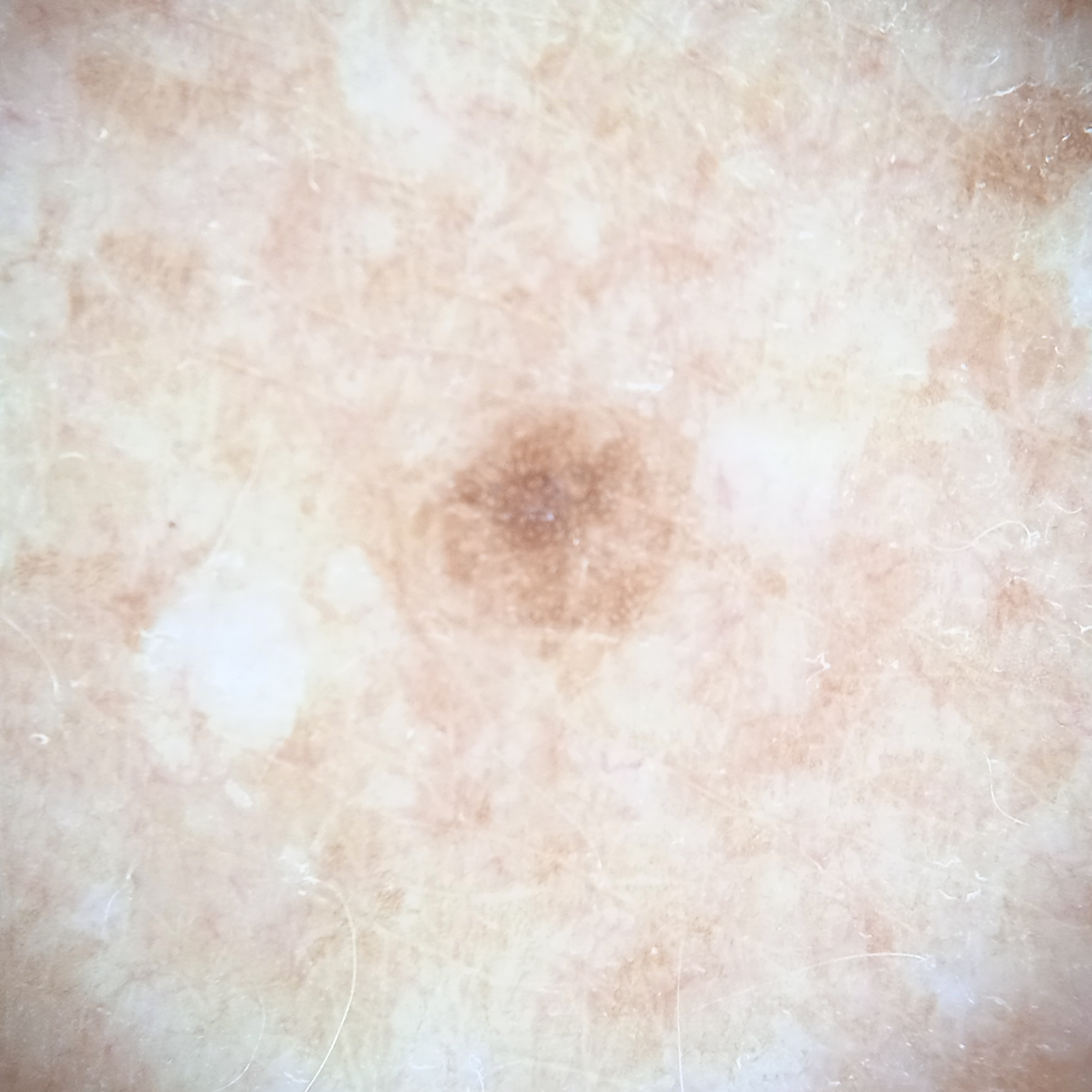Conclusion:
The dermatologists' assessment was a melanocytic nevus.